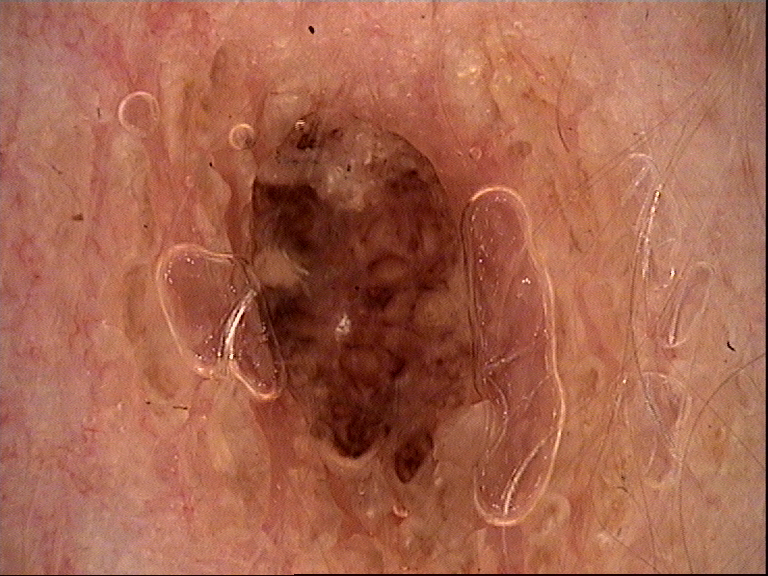Q: What was the diagnostic impression?
A: seborrheic keratosis (expert consensus)